A clinical photograph of a skin lesion; a female patient in their 60s — 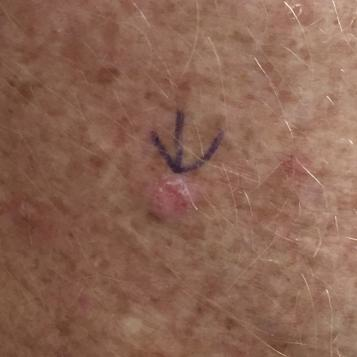Q: What is the anatomic site?
A: a thigh
Q: What was the clinical impression?
A: actinic keratosis (clinical consensus)